A female subject aged around 35; a contact-polarized dermoscopy image of a skin lesion — 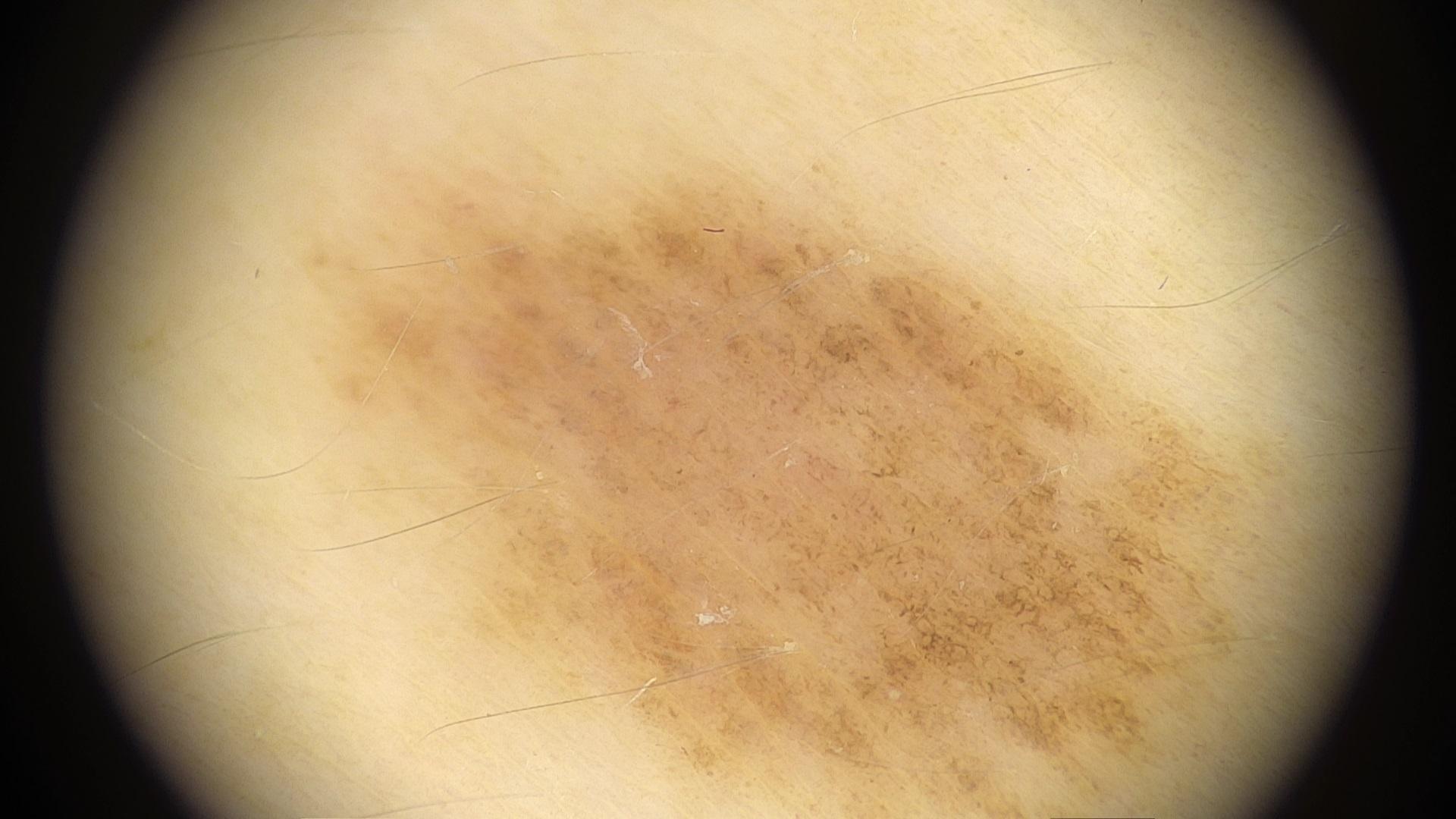Conclusion:
Clinically diagnosed as a nevus.